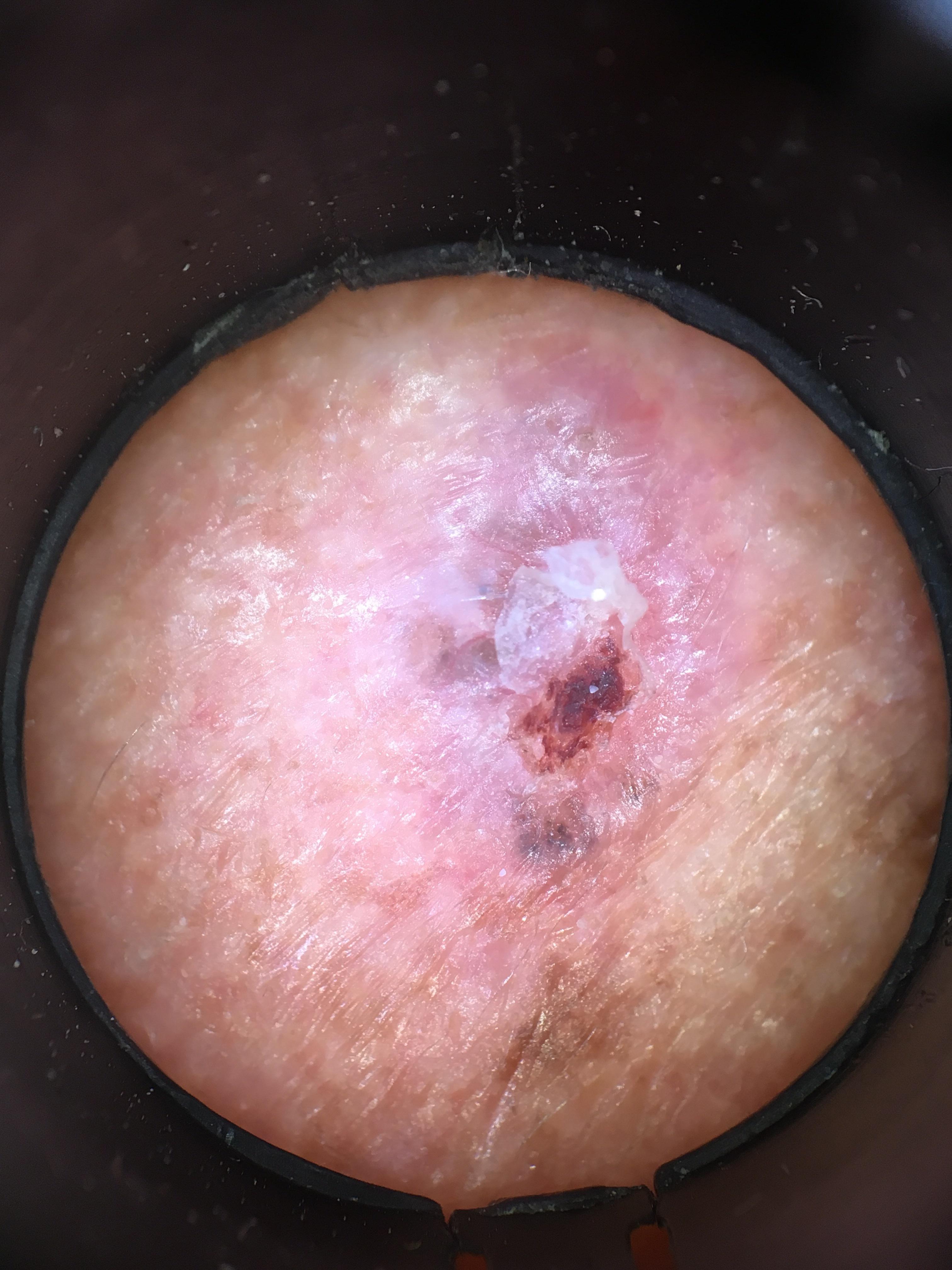A female patient aged 78 to 82. A dermoscopic close-up of a skin lesion. Skin type II. On biopsy, the diagnosis was a basal cell carcinoma.